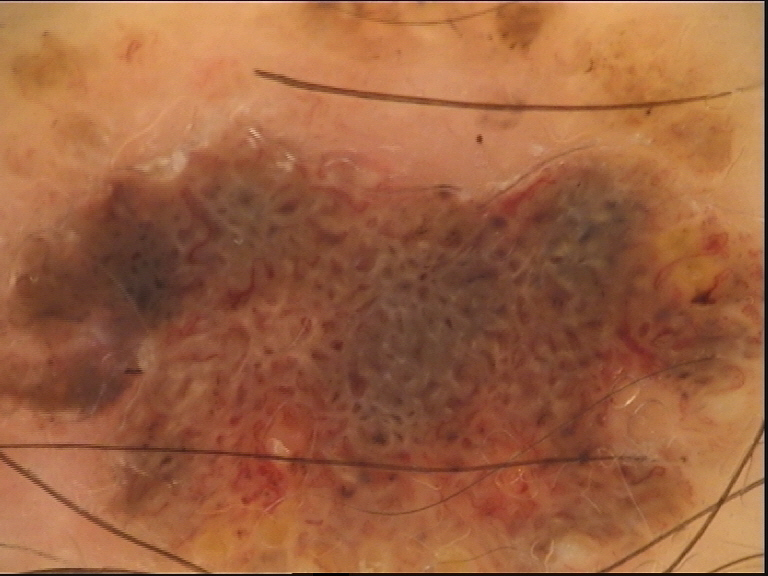{
  "diagnosis": {
    "name": "seborrheic keratosis",
    "code": "sk",
    "malignancy": "benign",
    "super_class": "non-melanocytic",
    "confirmation": "expert consensus"
  }
}